The lesion is described as raised or bumpy, symptoms reported: itching and enlargement, self-categorized by the patient as a nail problem, this image was taken at a distance, the patient reports the condition has been present for one to three months, the lesion involves the arm, the patient is female: 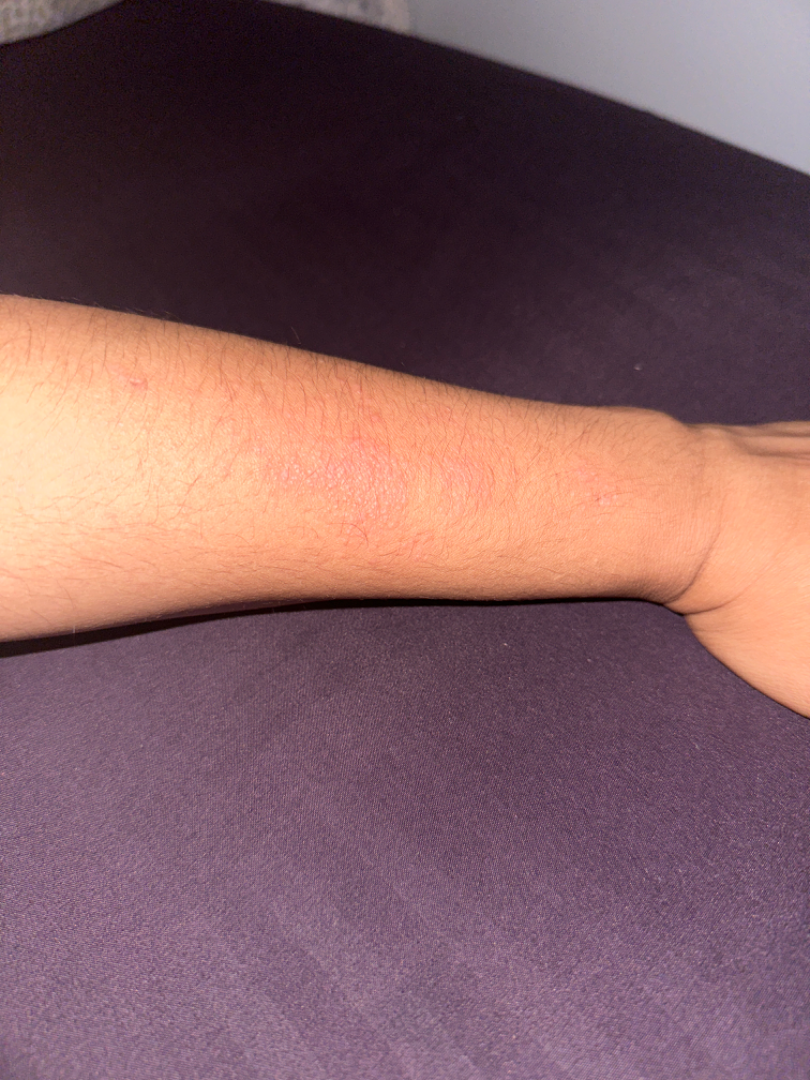differential = three independent reviewers: most likely Allergic Contact Dermatitis; also raised was Acute and chronic dermatitis; possibly Eczema; less probable is Lichen nitidus.